A clinical photo of a skin lesion taken with a smartphone:
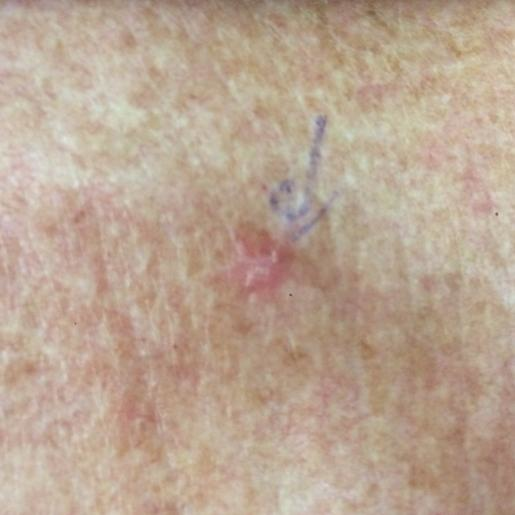location=the chest | symptoms=itching, growth | diagnostic label=actinic keratosis (clinical consensus).